The photo was captured at an angle; the back of the torso, leg and front of the torso are involved; the contributor is a female aged 18–29 — 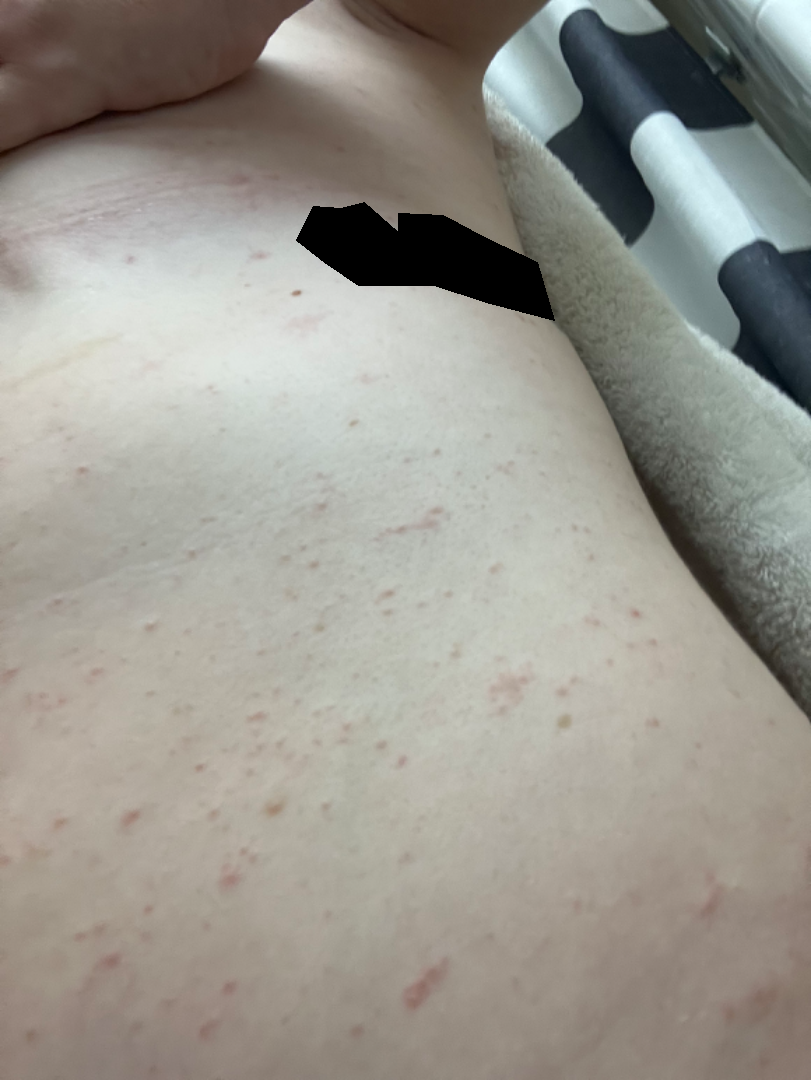<case>
  <differential>
    <leading>Urticaria</leading>
  </differential>
</case>